The affected area is the palm; the photograph was taken at a distance; the lesion is associated with itching, bleeding, enlargement, darkening, bothersome appearance, burning and pain; the patient described the issue as a rash; the condition has been present for more than one year; the lesion is described as fluid-filled and rough or flaky — 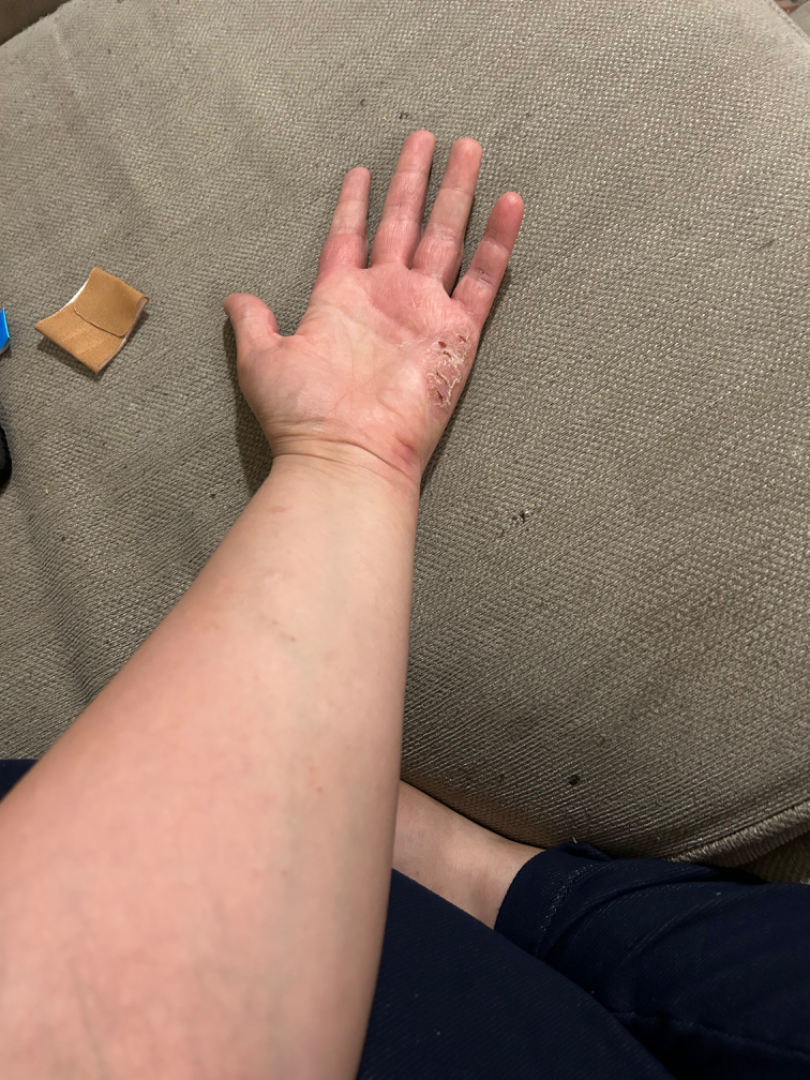On remote dermatologist review, favoring Irritant Contact Dermatitis; also on the differential is Psoriasis; also consider Allergic Contact Dermatitis.